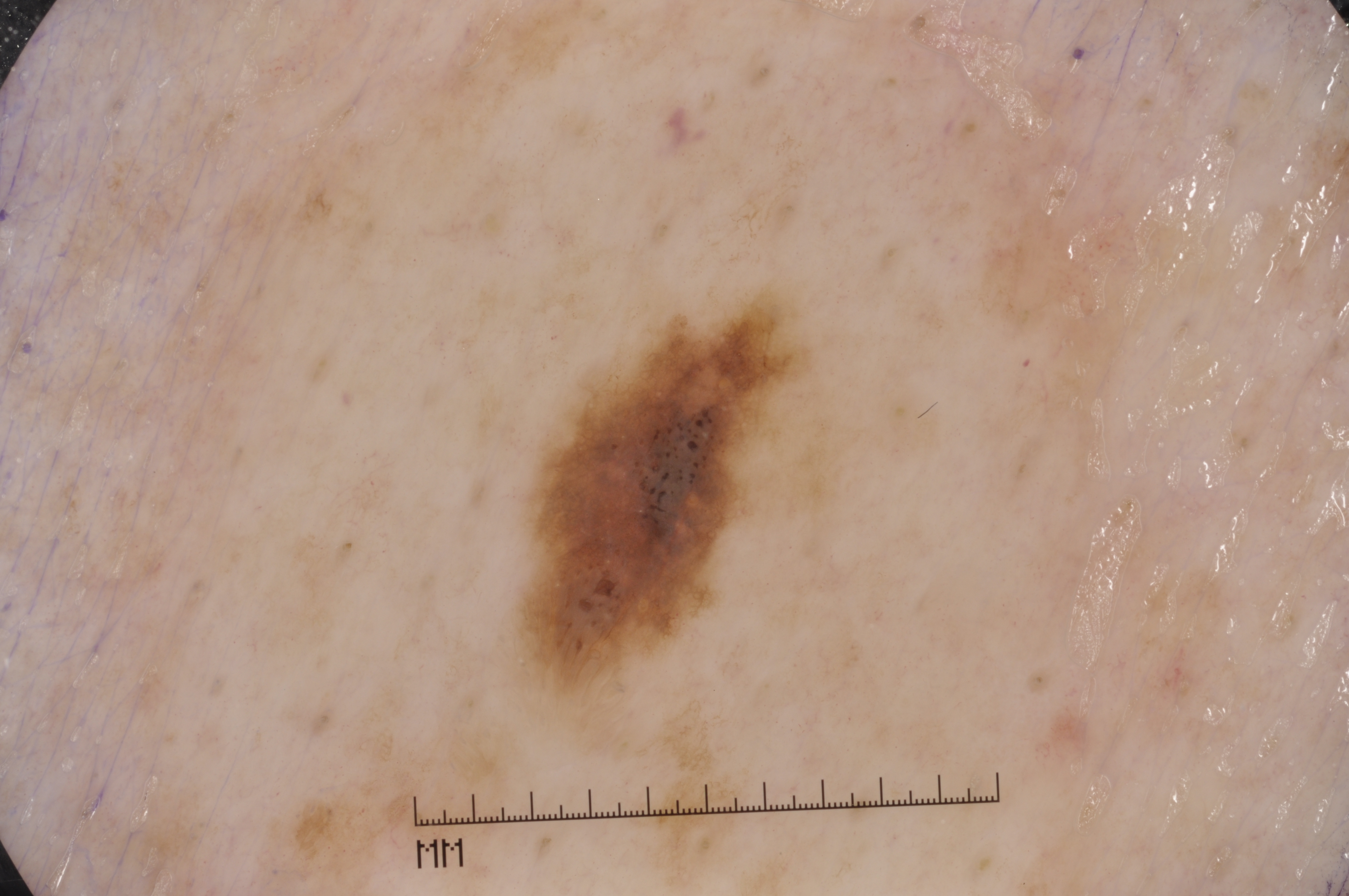A male patient, aged around 65. A skin lesion imaged with a dermatoscope. Dermoscopic review identifies pigment network and milia-like cysts; no negative network or streaks. The lesion takes up about 5% of the image. In (x1, y1, x2, y2) order, the lesion's extent is 527/309/801/672. Expert review diagnosed this as a melanocytic nevus.